A clinical close-up photograph of a skin lesion; a female patient 58 years of age:
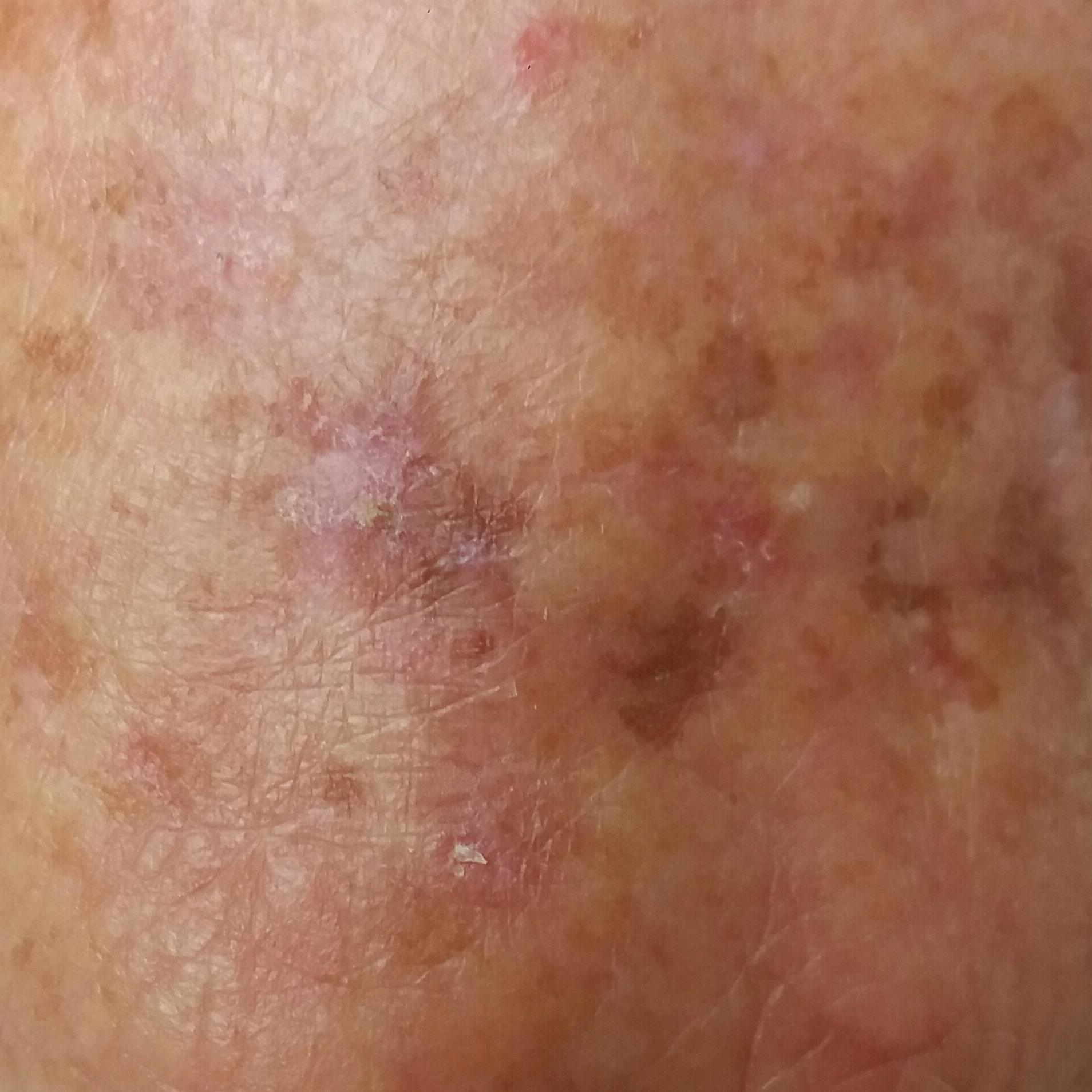Q: What is the anatomic site?
A: a hand
Q: What is this lesion?
A: actinic keratosis (clinical consensus)